Dermoscopy of a skin lesion.
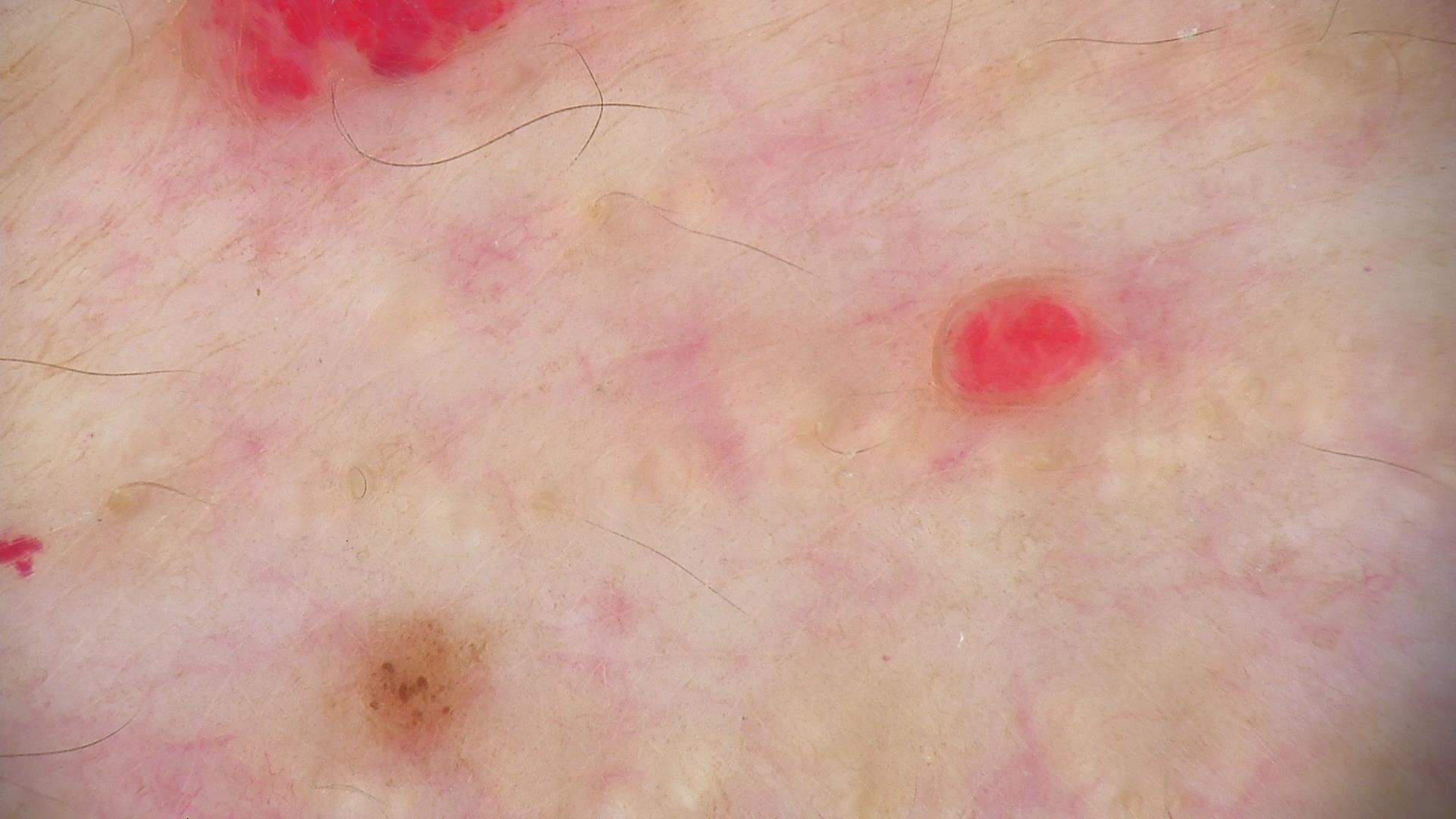Labeled as a benign, vascular lesion — a hemangioma.